The condition has been present for one to four weeks, the patient notes itching, self-categorized by the patient as a rash, a close-up photograph, located on the arm and back of the torso.
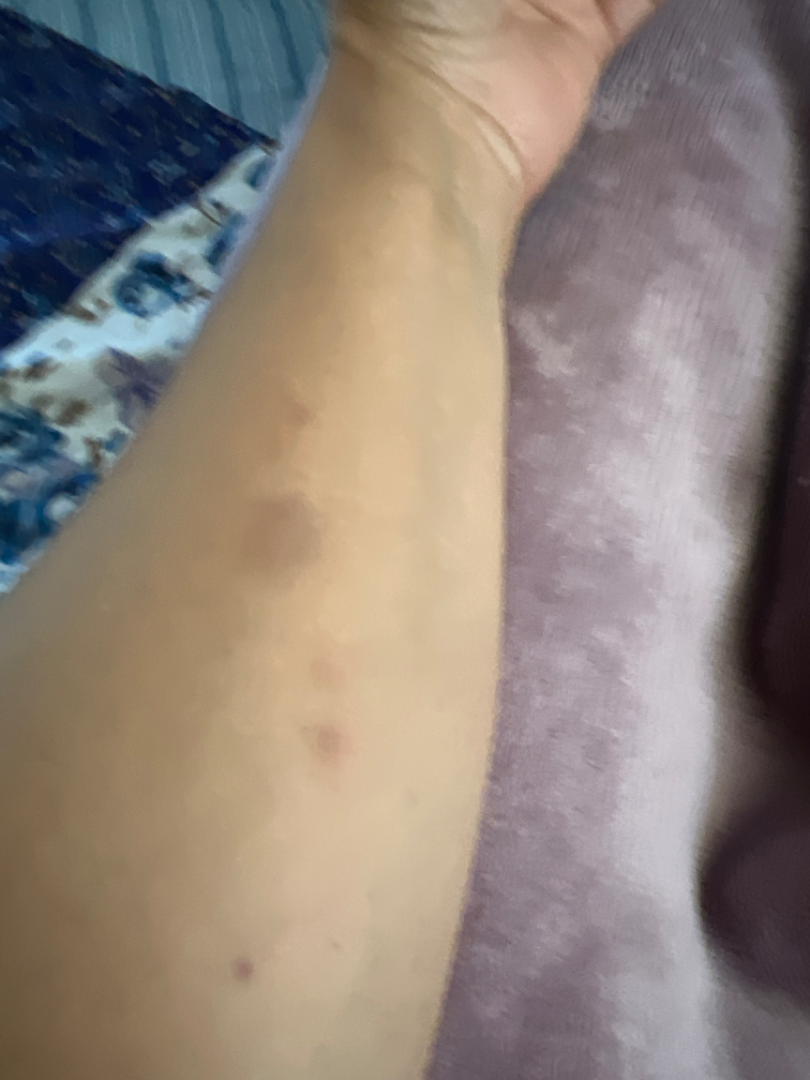Diagnostic features were not clearly distinguishable in this photograph.